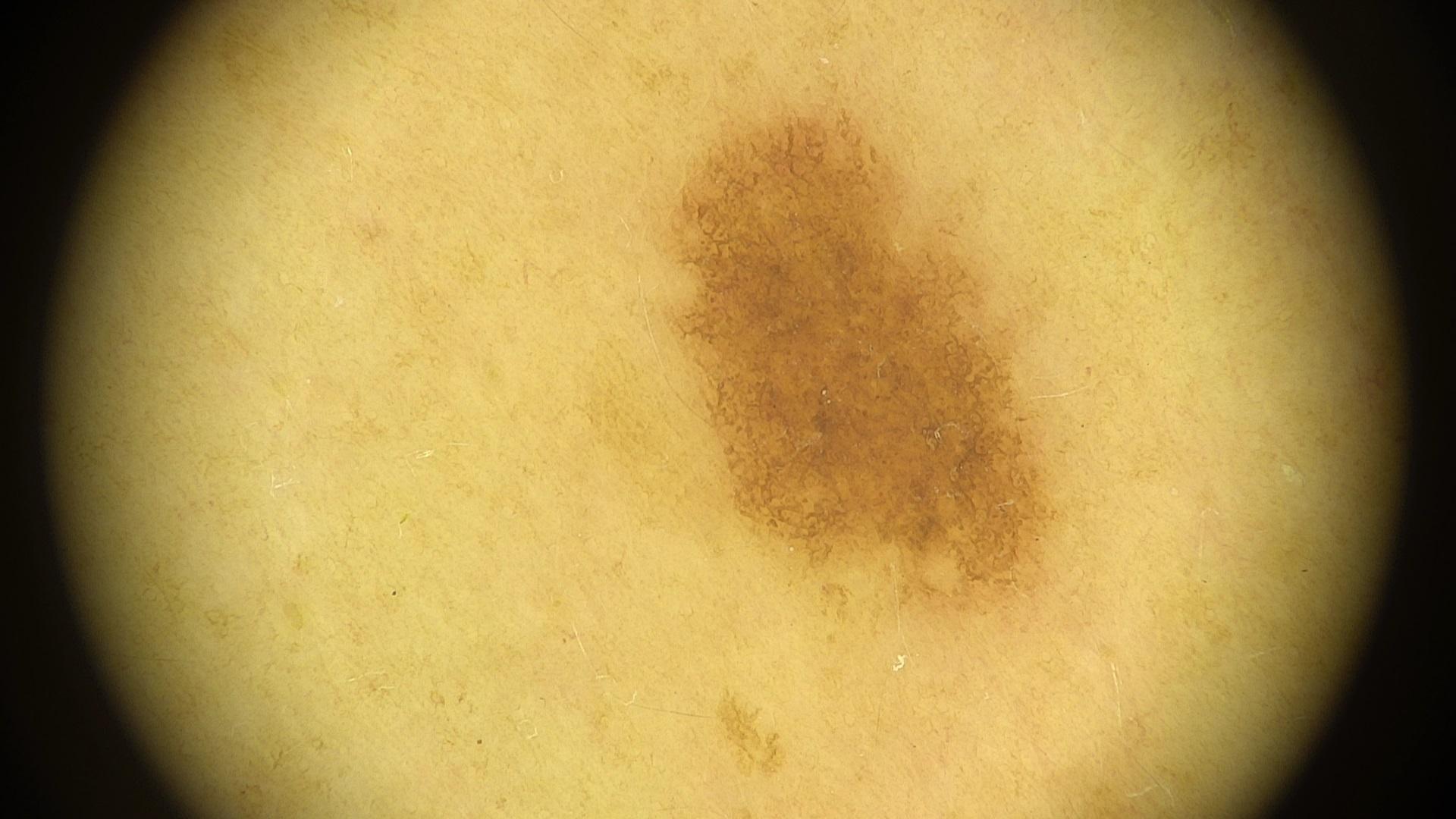skin phototype = II
relevant background = no melanoma in first-degree relatives and no prior melanoma
image = dermatoscopic image
location = the trunk
assessment = Nevus